A dermoscopic view of a skin lesion.
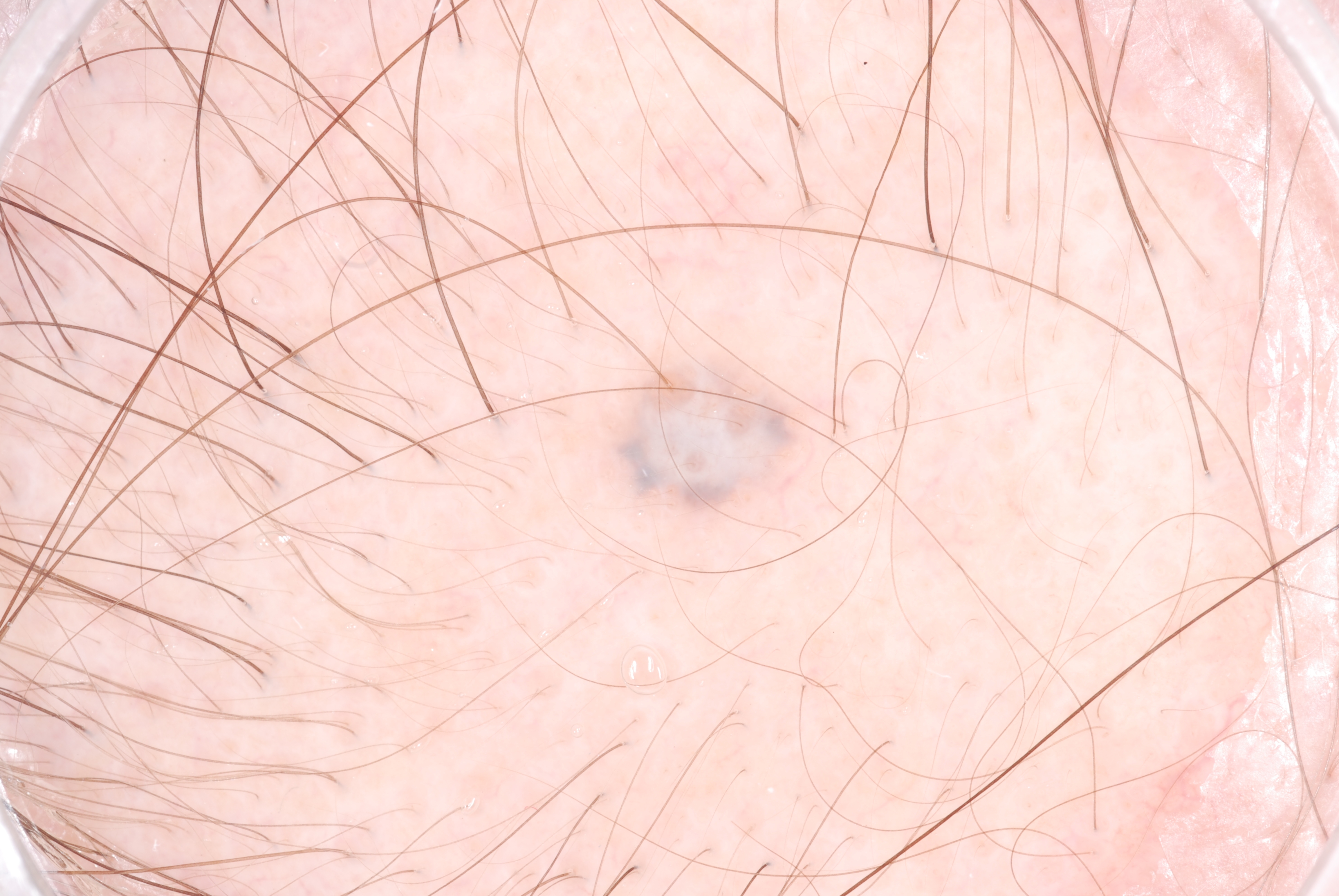As (left, top, right, bottom), the lesion's extent is <bbox>597, 355, 814, 529</bbox>.
Expert review diagnosed this as a melanocytic nevus.